A dermoscopic photograph of a skin lesion.
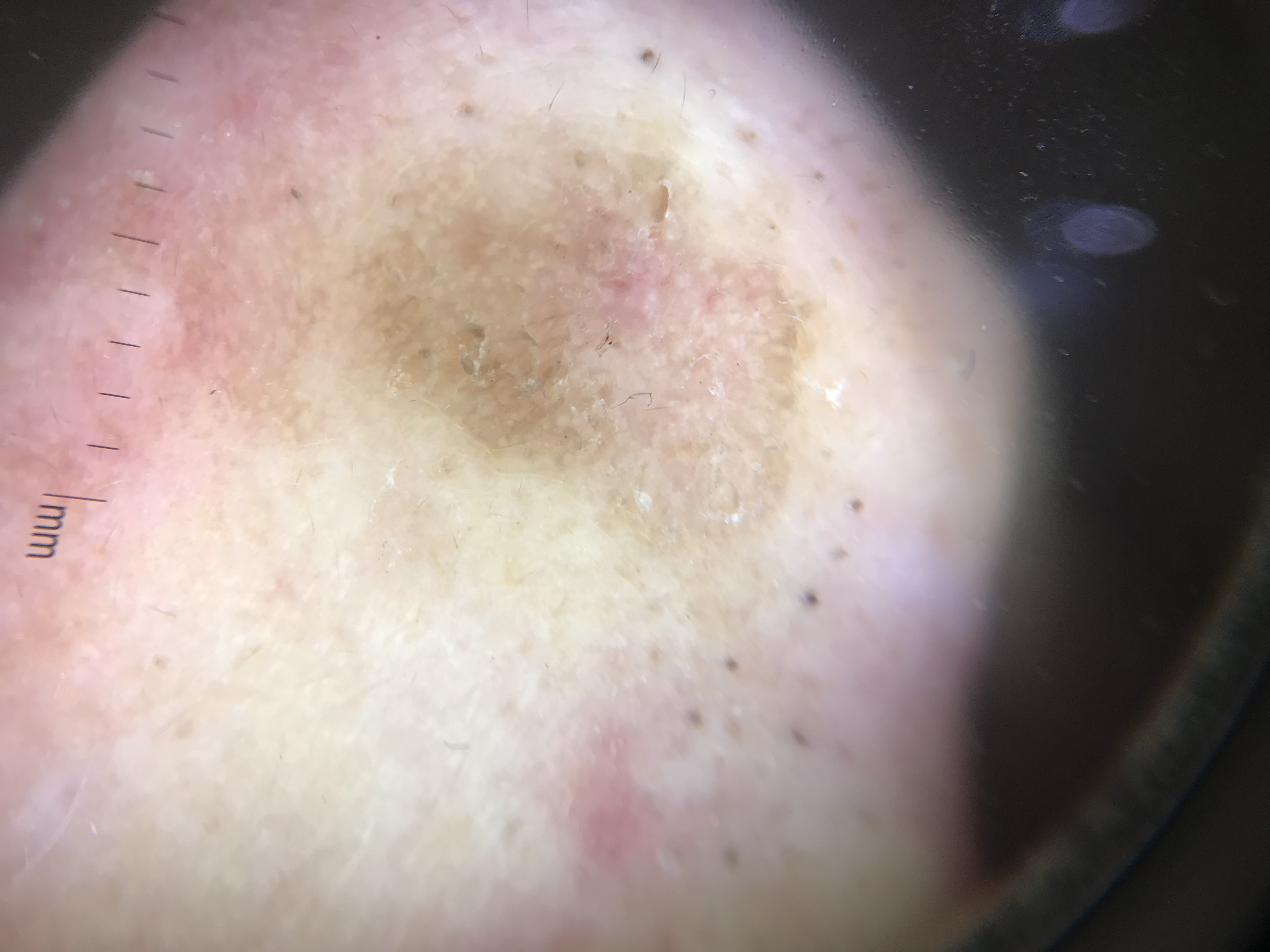Conclusion:
Classified as a keratinocytic lesion — a seborrheic keratosis.